The lesion involves the arm, the photograph was taken at an angle, the subject is a male aged 18–29.
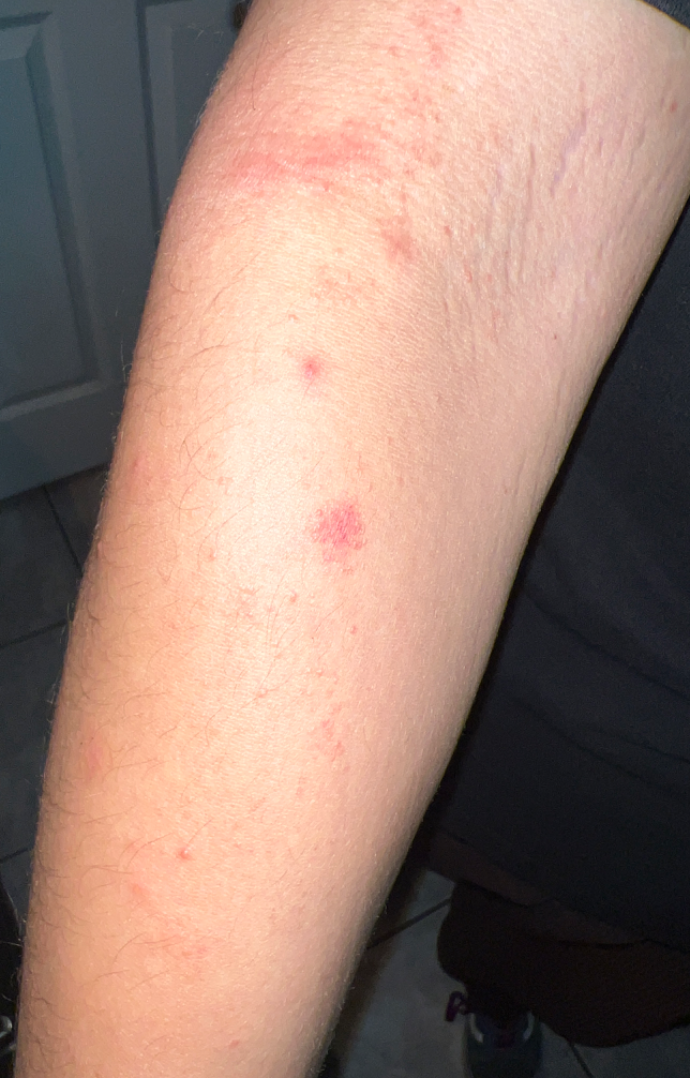- onset — one to four weeks
- texture — raised or bumpy
- systemic symptoms — none reported
- self-categorized as — a rash
- lesion symptoms — bothersome appearance and itching
- dermatologist impression — favoring Eczema; also consider Irritant Contact Dermatitis; less likely is Allergic Contact Dermatitis; less probable is Hypersensitivity